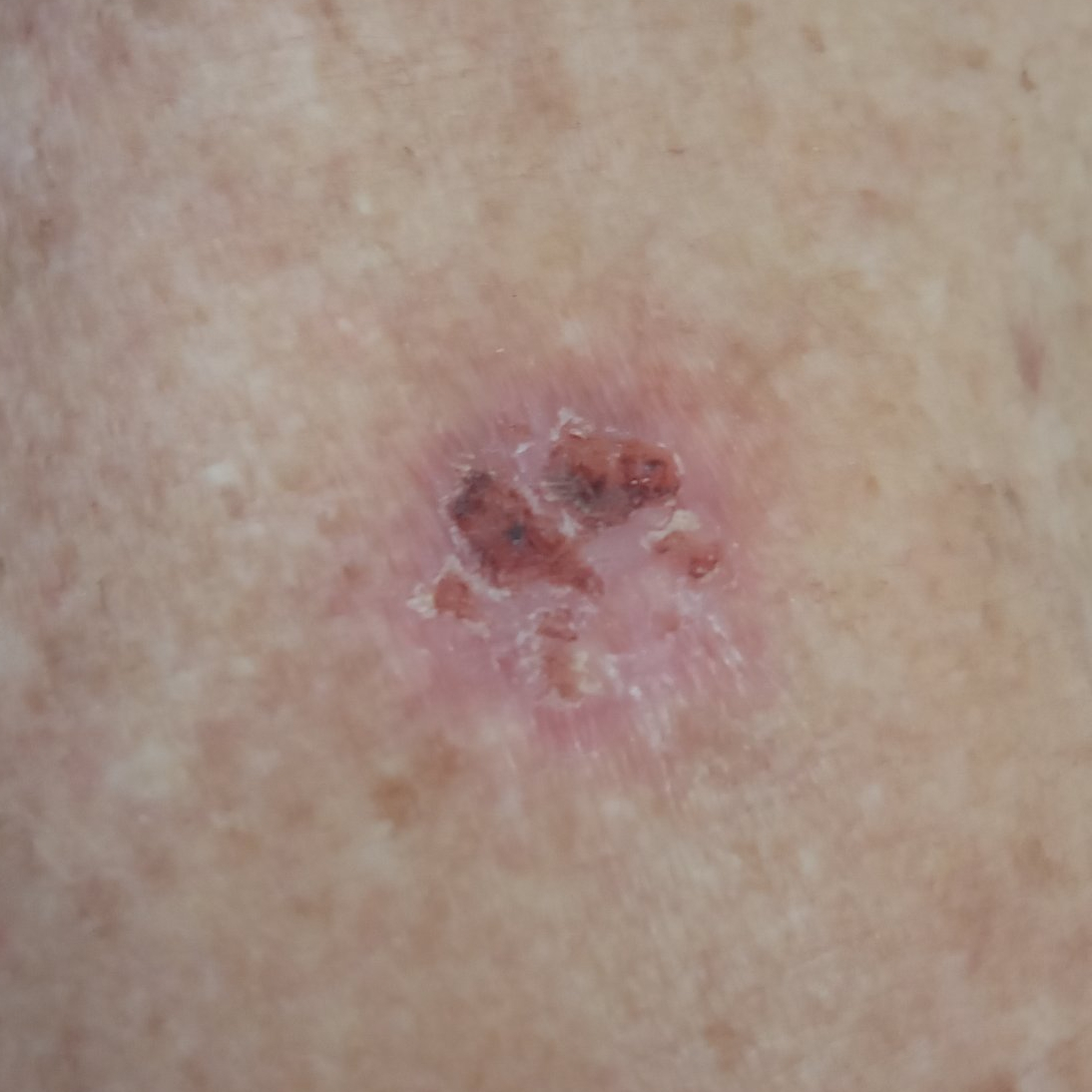A male patient 72 years of age.
The patient was assessed as Fitzpatrick phototype II.
The lesion involves the chest.
The patient reports that the lesion itches, hurts, has grown, has bled, and is elevated, but has not changed.
Biopsy-confirmed as a malignancy — a basal cell carcinoma.